An image taken at an angle · the arm is involved:
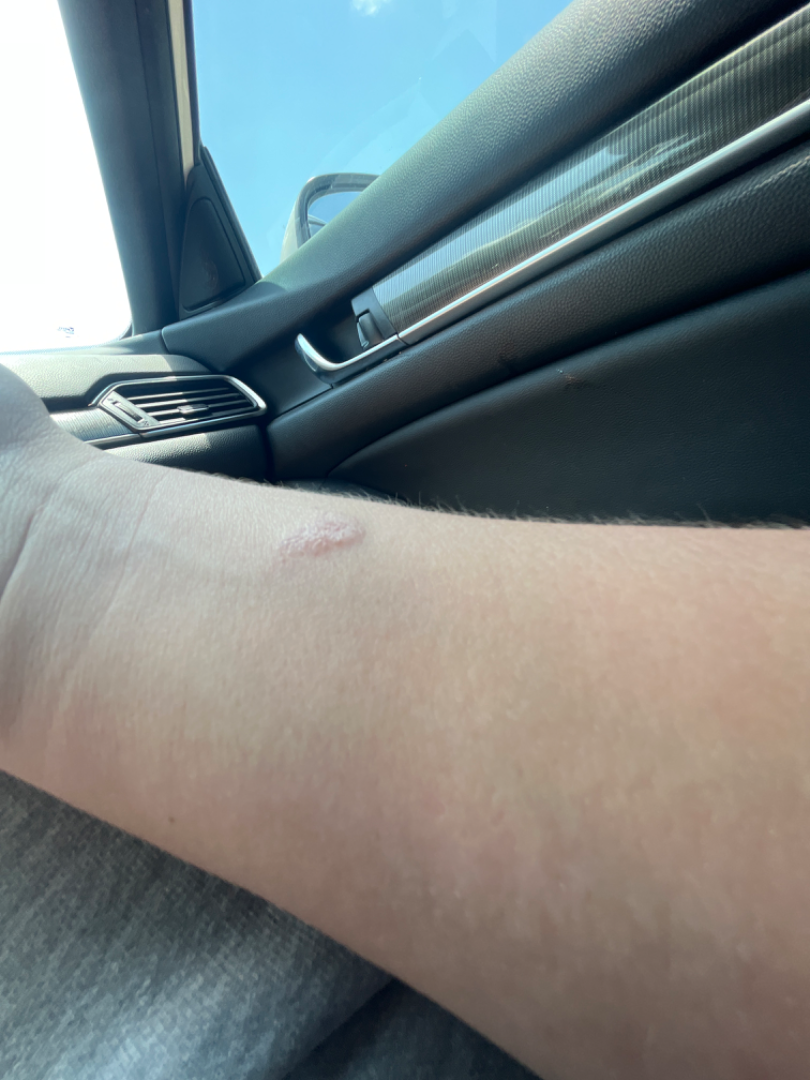The reviewer was unable to grade this case for skin condition.
Lay graders estimated Monk Skin Tone 1 or 3 (two reviewer pools disagreed).
The lesion is associated with itching.
The lesion is described as raised or bumpy.
The contributor notes the condition has been present for less than one week.